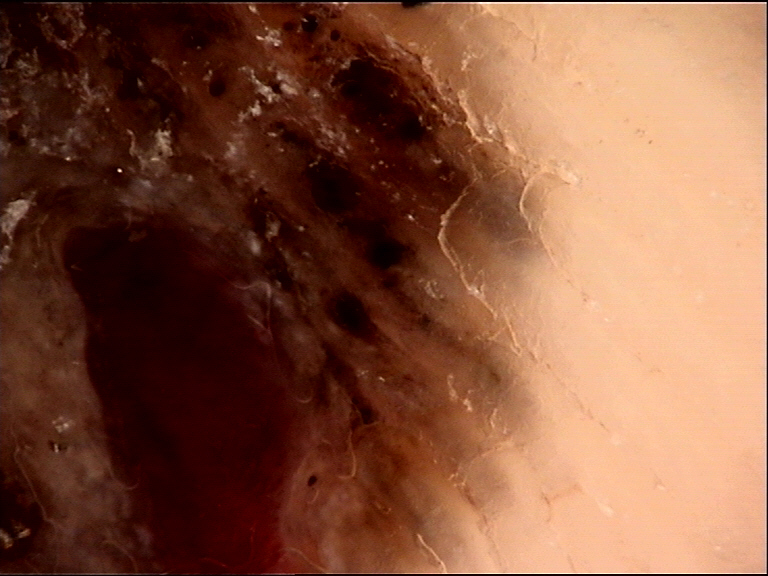Conclusion: The biopsy diagnosis was an acral nodular melanoma.